The patient says their skin reddens with sun exposure · dermoscopy of a skin lesion · the patient describes having a moderate number of moles · a female patient 50 years of age · on a questionnaire the patient reported a personal history of skin cancer:
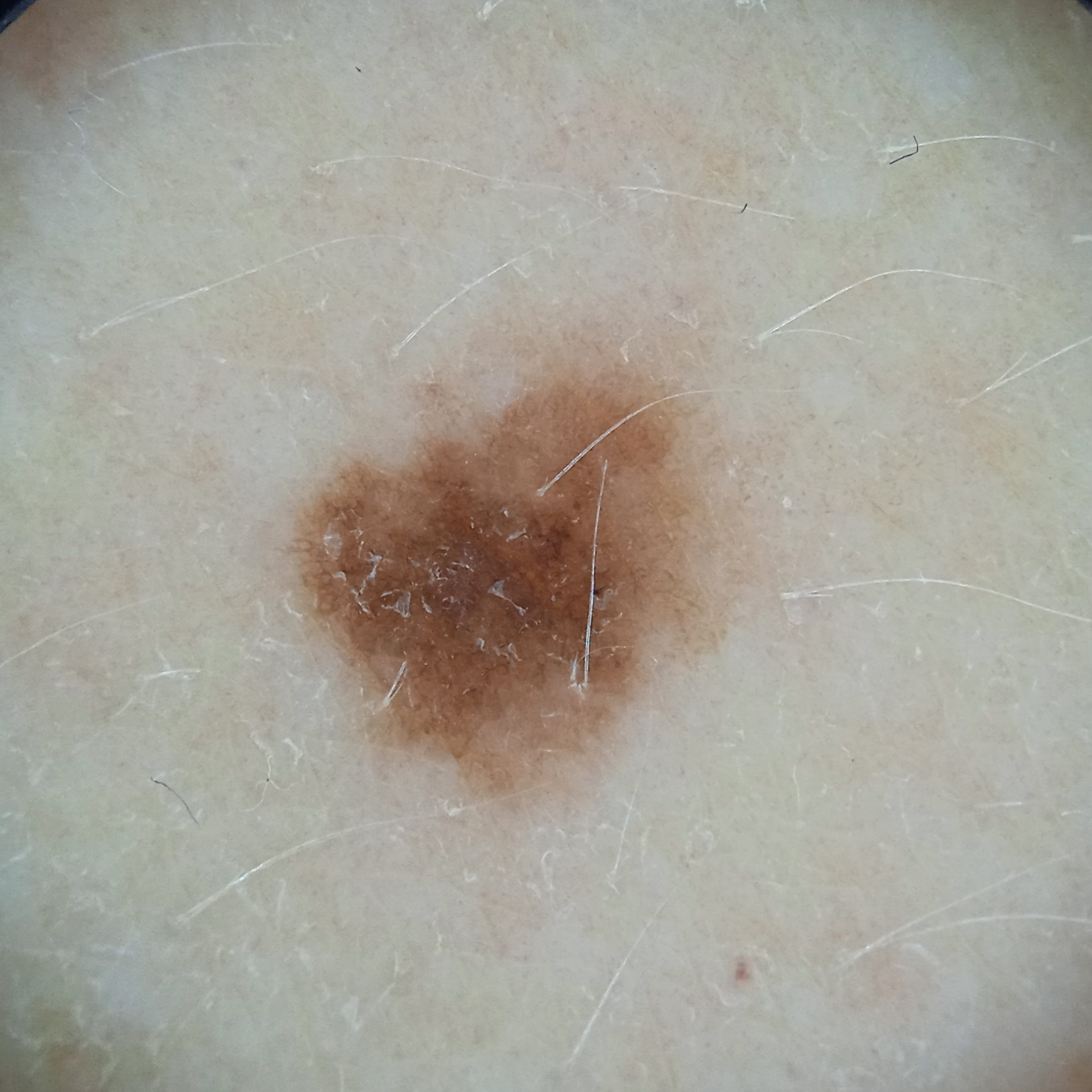Findings:
The lesion is located on the torso. Measuring roughly 5.4 mm.
Assessment:
Dermatologist review favored a melanocytic nevus.